A dermatoscopic image of a skin lesion: 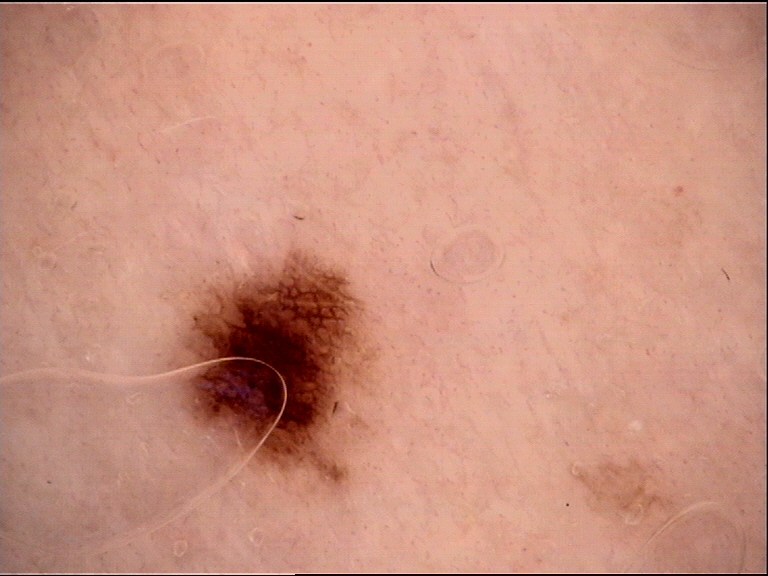Q: What is the diagnosis?
A: dysplastic junctional nevus (expert consensus)